A female subject in their 50s; the patient is Fitzpatrick III; history notes prior malignancy (patient or family); a clinical close-up photograph of a skin lesion:
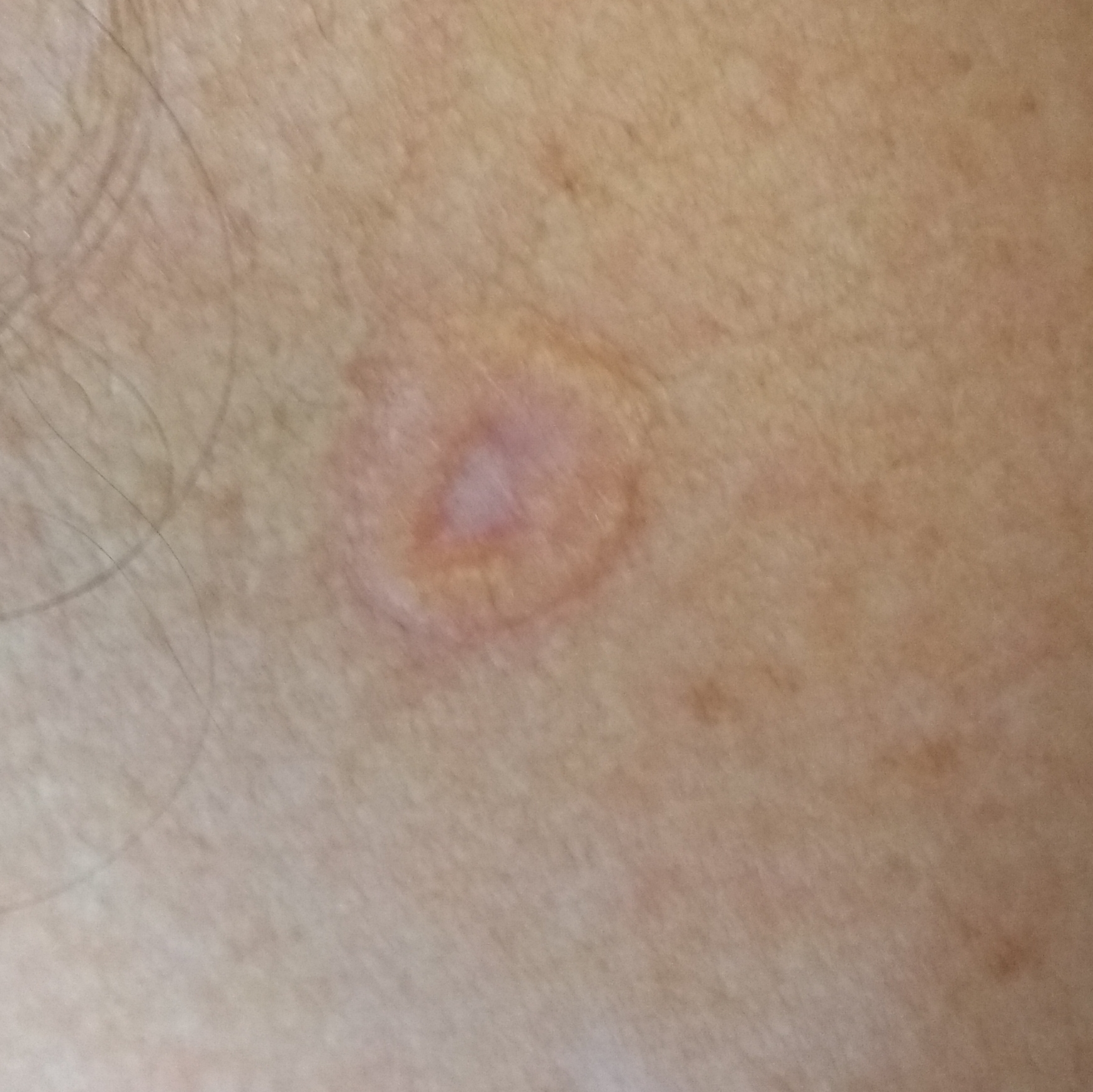The lesion is on the neck. The lesion is roughly 18 by 10 mm. The patient describes that the lesion is elevated. Histopathologically confirmed as a basal cell carcinoma.